A dermoscopy image of a single skin lesion:
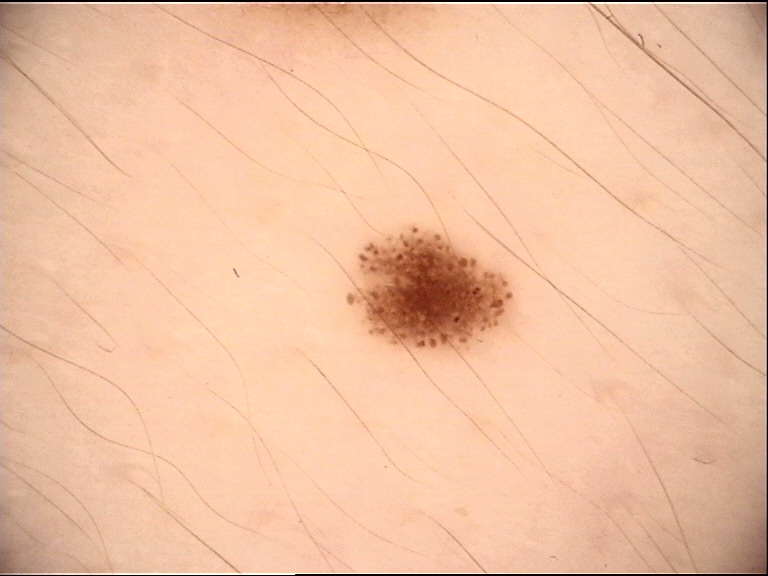The diagnostic label was a benign lesion — a dysplastic junctional nevus.